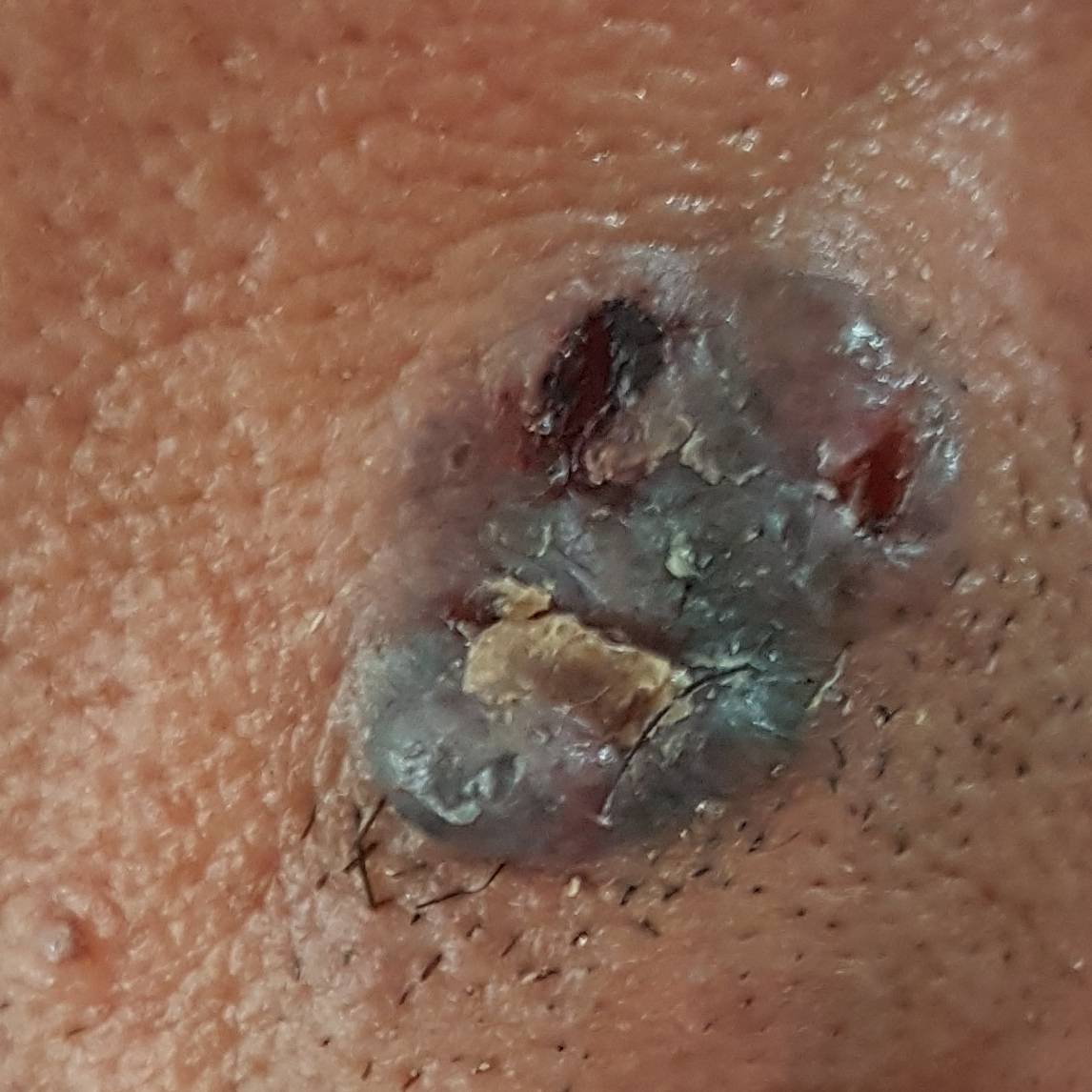  risk_factors:
    positive:
      - prior cancer (patient or family)
      - pesticide exposure
      - alcohol use
  patient:
    age: 37
    gender: male
  skin_type: V
  lesion_location: the face
  symptoms:
    present:
      - elevation
      - bleeding
      - growth
      - itching
      - pain
  diagnosis:
    name: basal cell carcinoma
    code: BCC
    malignancy: malignant
    confirmation: histopathology